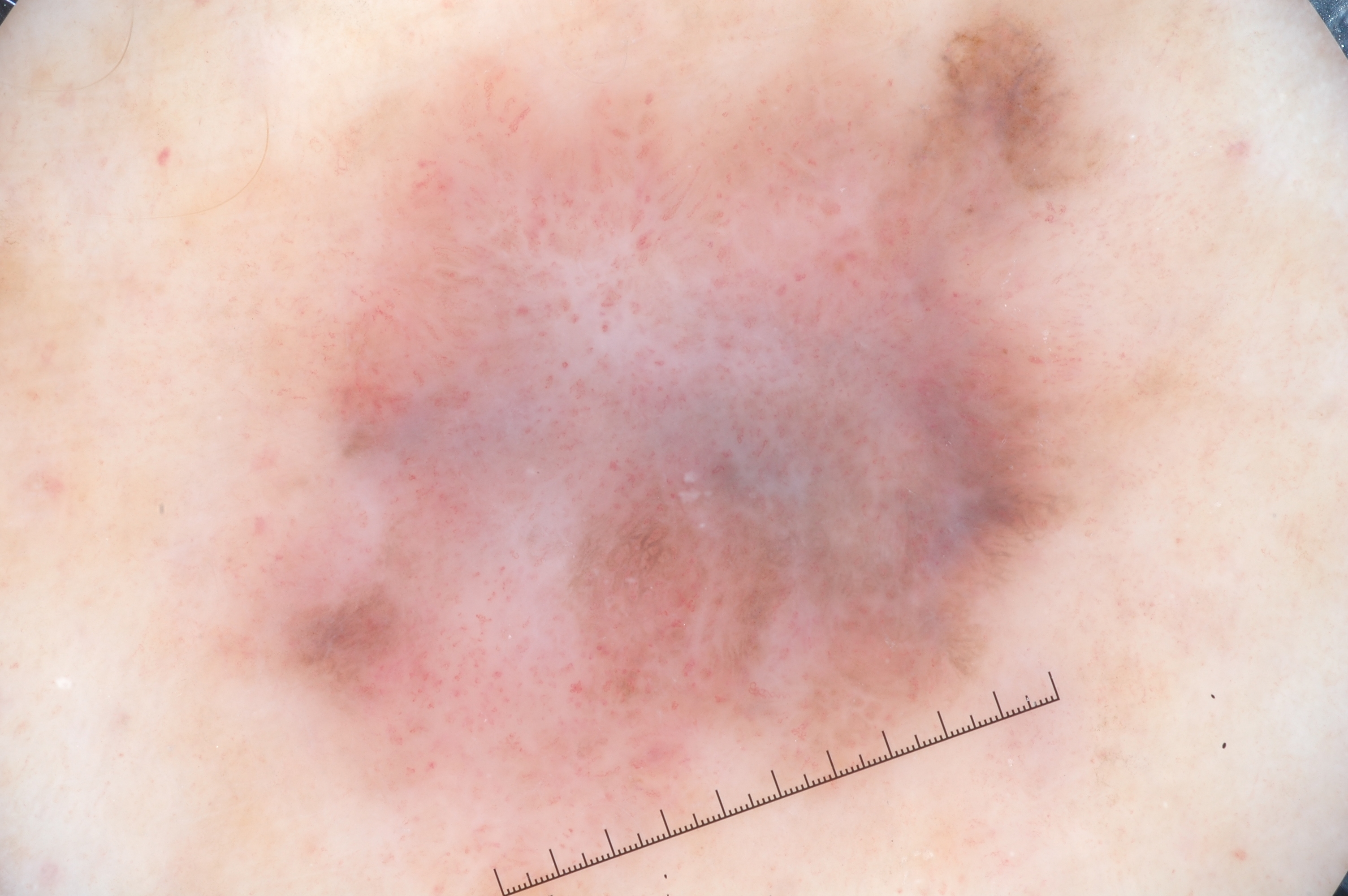A dermoscopic close-up of a skin lesion. A male patient aged approximately 65. The lesion takes up about 54% of the image. As (left, top, right, bottom), the lesion occupies the region 190/0/1190/895. Dermoscopy demonstrates pigment network and negative network. Histopathological examination showed a melanoma.